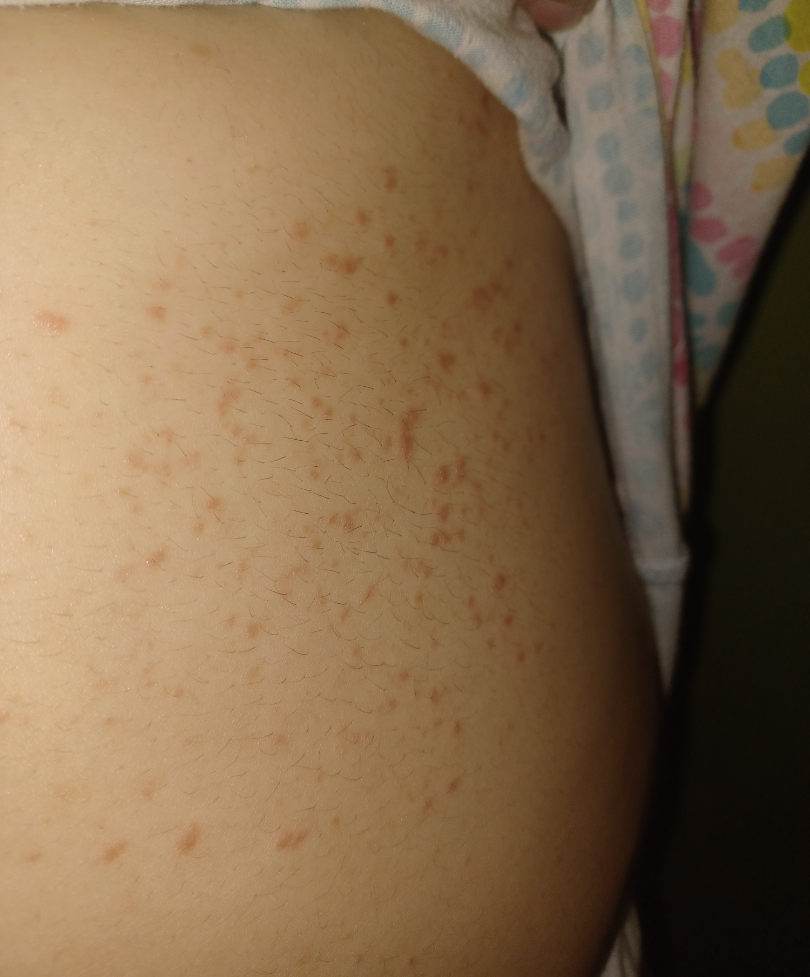| field | value |
|---|---|
| systemic symptoms | none reported |
| image framing | at an angle |
| surface texture | raised or bumpy |
| patient's own categorization | a rash |
| site | front of the torso |
| patient | female |
| reported symptoms | darkening and bothersome appearance |
| assessment | Eczema (considered); Grover's disease (considered); Miliaria (remote); Folliculitis (remote) |